Dermoscopy of a skin lesion. The patient describes having a moderate number of moles. A female subject 32 years of age. The patient reports a personal history of cancer, a personal history of skin cancer, no family history of skin cancer, and no sunbed use. The patient says their skin reddens with sun exposure: 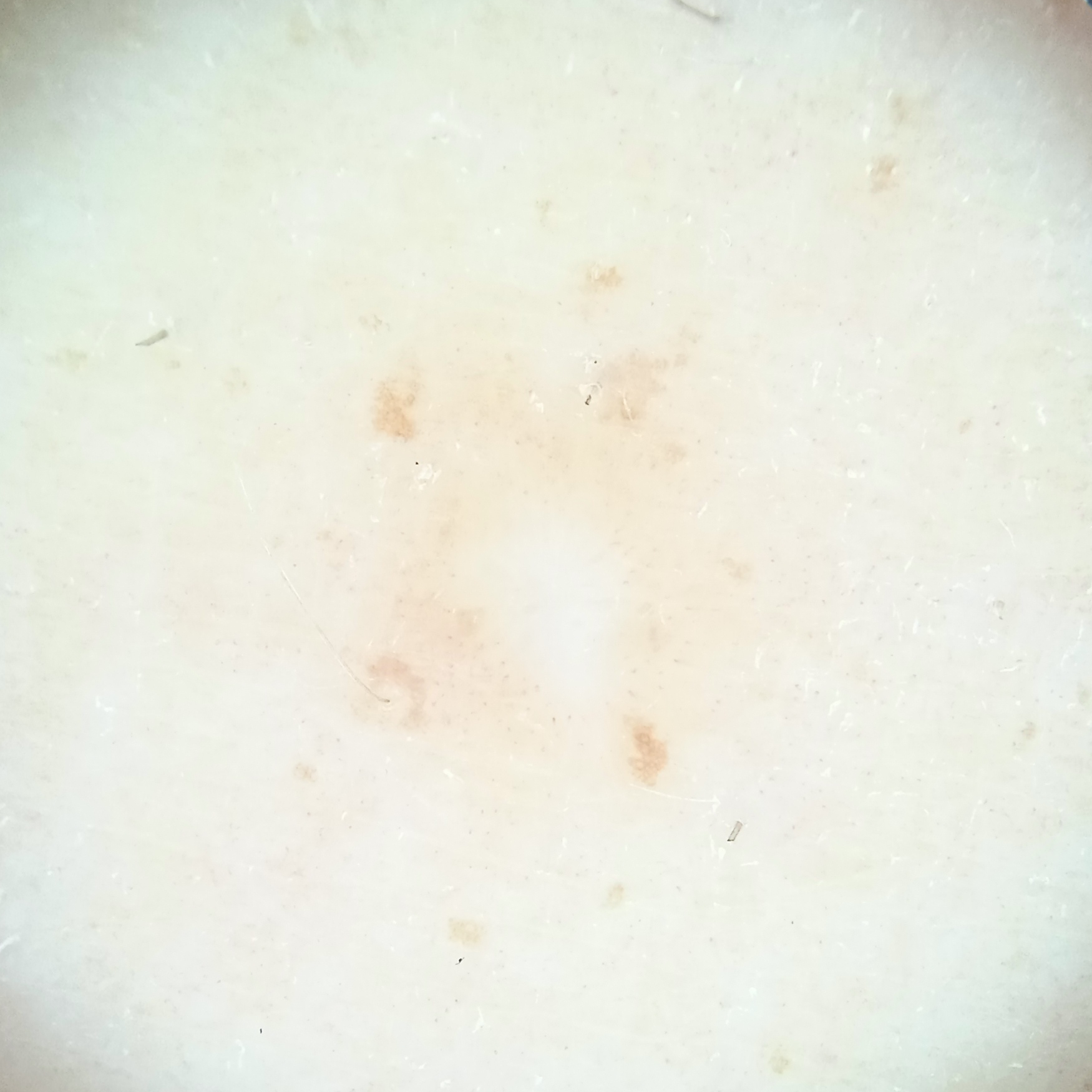{"lesion_size": {"diameter_mm": 5.4}, "diagnosis": {"name": "dermatofibroma", "malignancy": "benign"}}